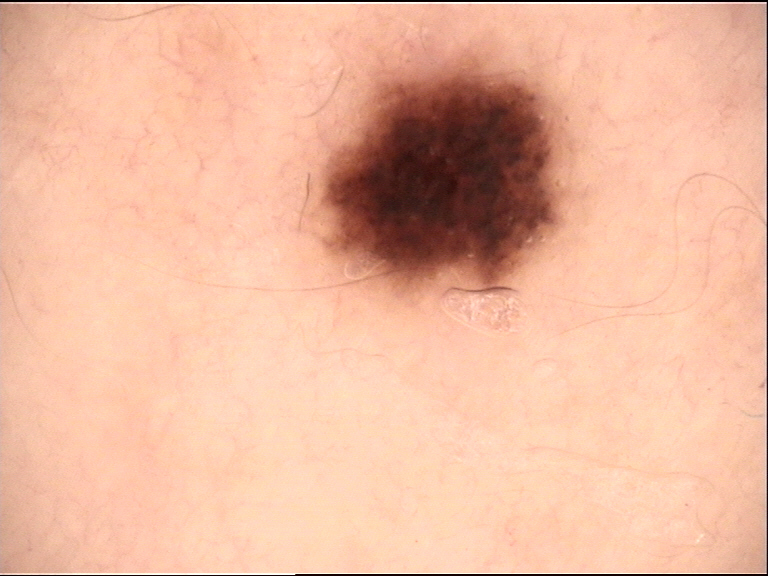Q: What is the diagnosis?
A: junctional nevus (expert consensus)